The lesion involves the leg. The photo was captured at a distance.
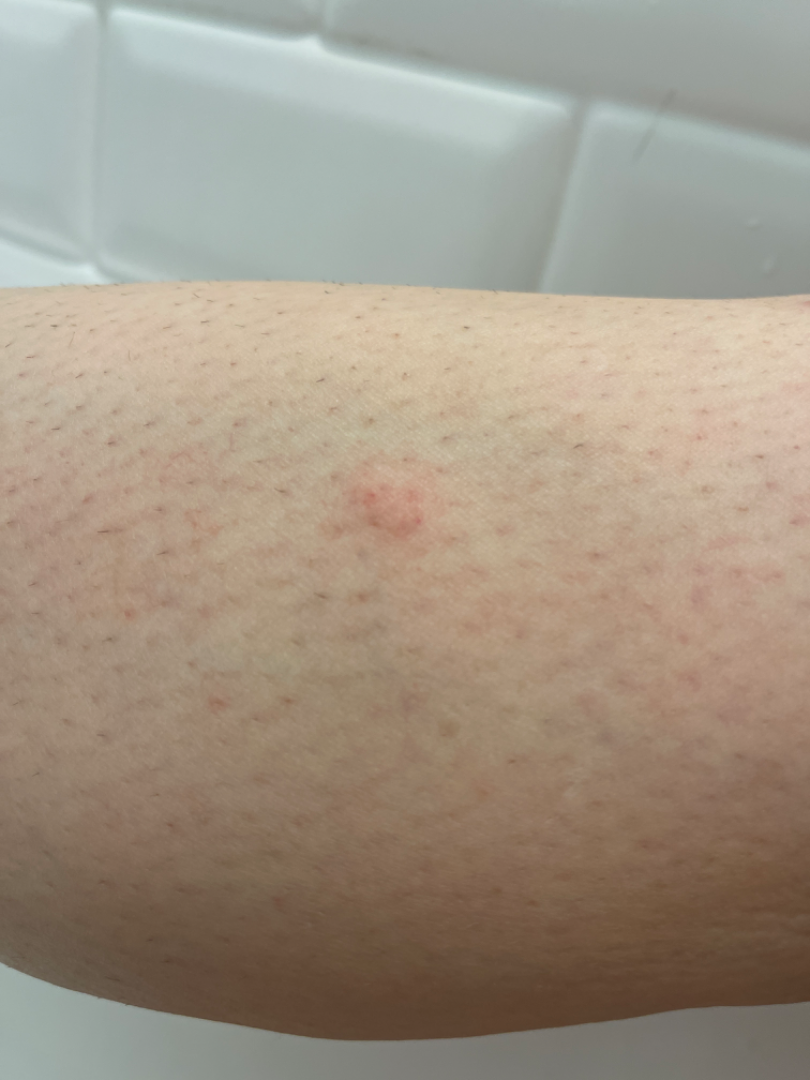Findings: Diagnostic features were not clearly distinguishable in this photograph.